No relevant systemic symptoms. The patient described the issue as a rash. Reported duration is about one day. The lesion is described as raised or bumpy. The affected area is the leg. Close-up view. The lesion is associated with itching. The subject is male.
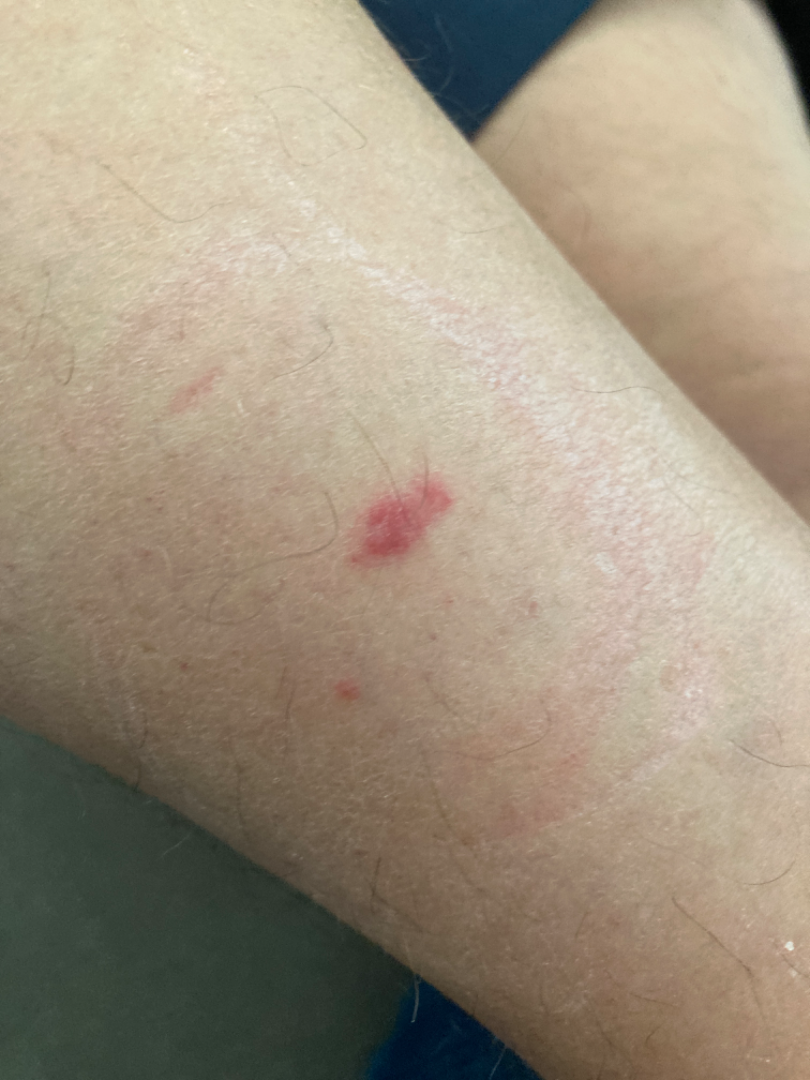assessment = Eczema (0.33); Allergic Contact Dermatitis (0.33); Basal Cell Carcinoma (0.33).